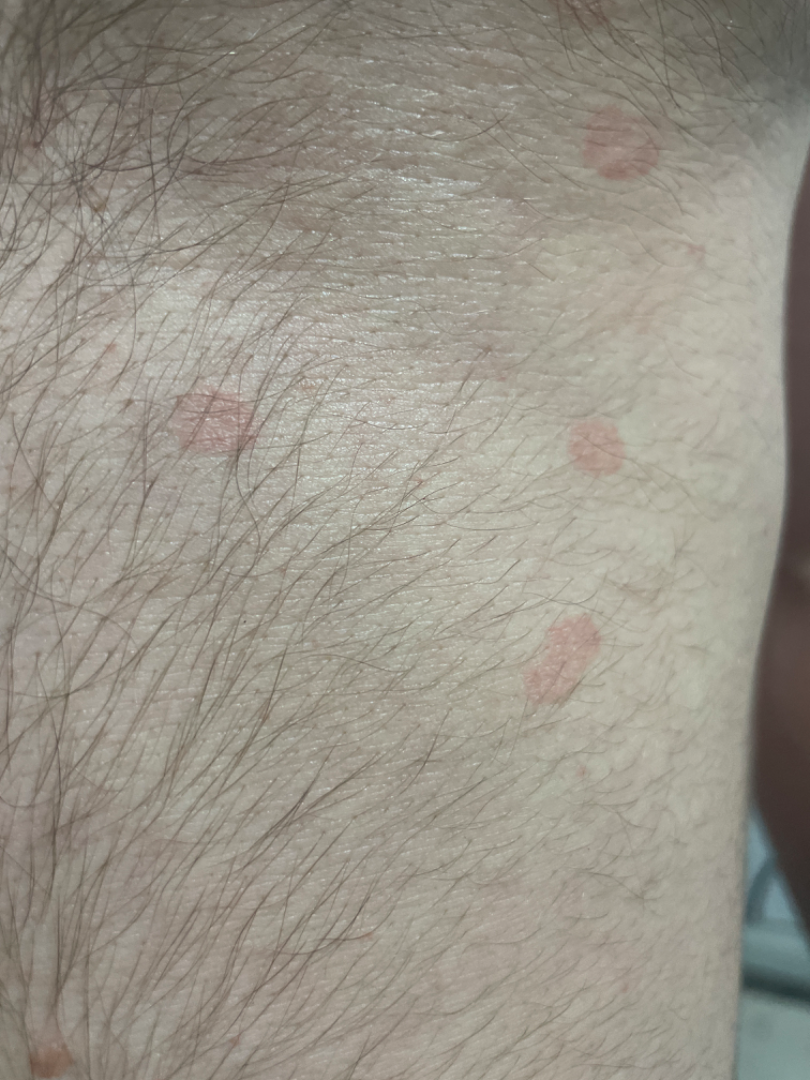| field | value |
|---|---|
| skin tone | Fitzpatrick skin type II; lay graders estimated a Monk skin tone scale of 3 |
| photo taken | at an angle |
| dermatologist impression | reviewed remotely by one dermatologist: favoring Eczema; an alternative is Pityriasis rosea; less likely is Psoriasis |